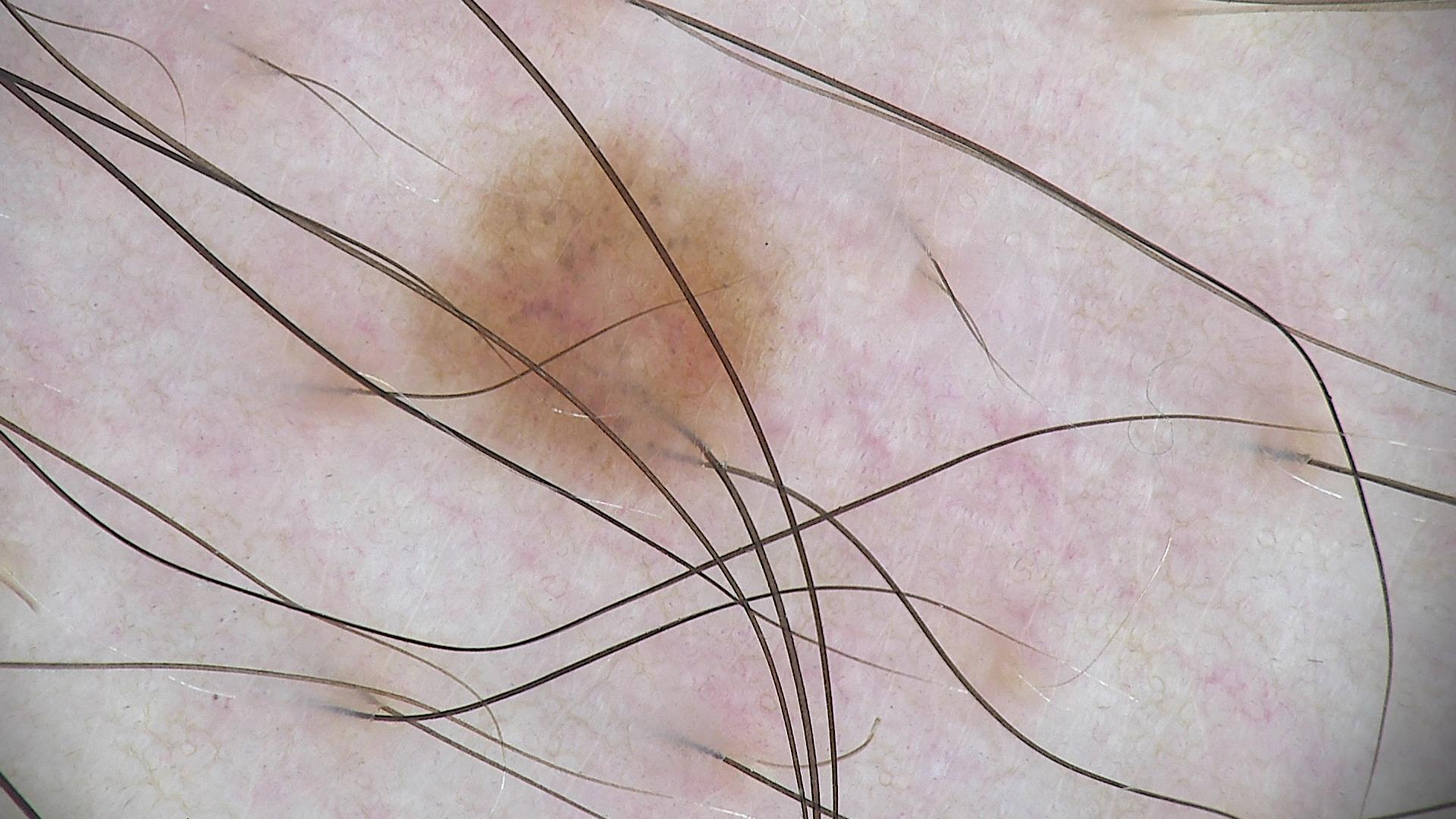Summary:
A dermoscopic close-up of a skin lesion.
Impression:
Labeled as a benign lesion — a dysplastic junctional nevus.